Numerous moles by the patient's own estimate. The patient says their skin reddens with sun exposure. By self-report, a history of sunbed use. A clinical photograph of a skin lesion. Acquired for a research image collection, with no referral diagnosis. A female patient age 26 — 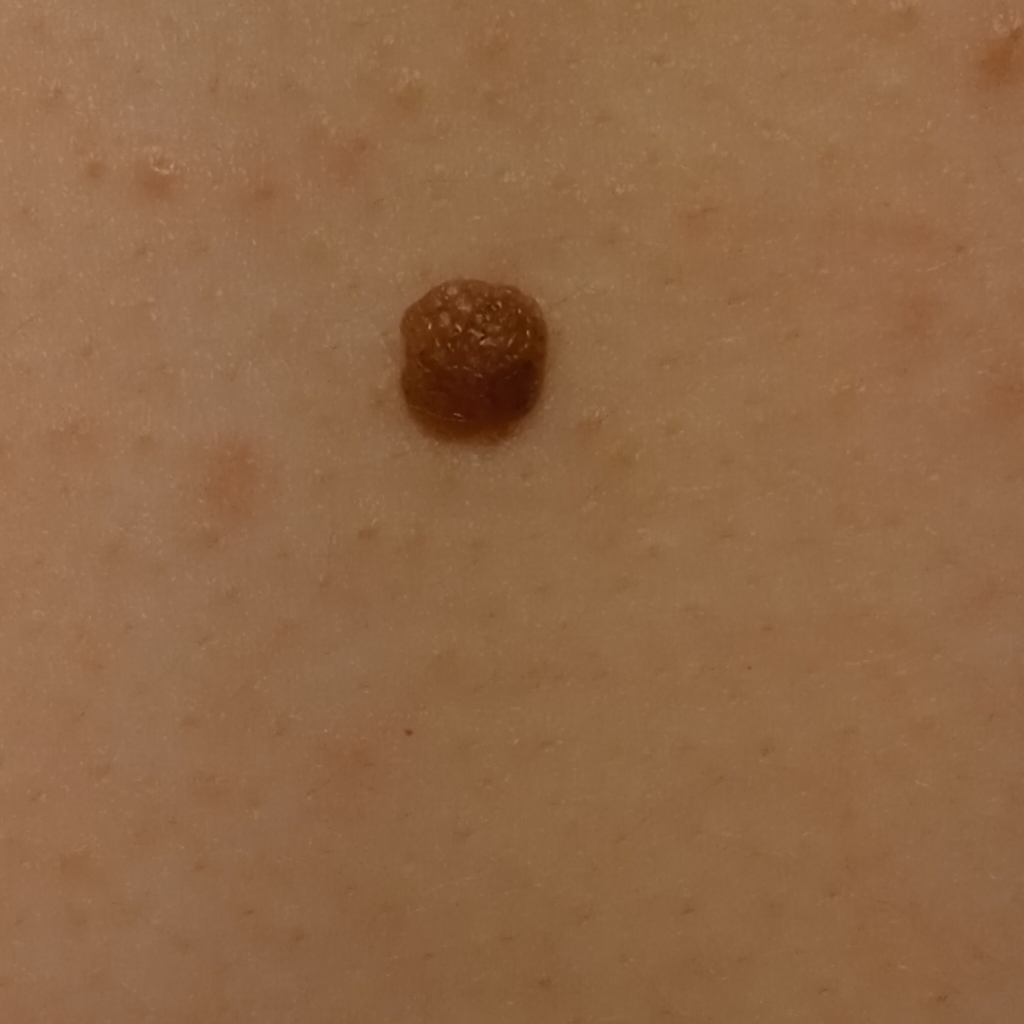The lesion is located on the back.
The lesion is about 5.6 mm across.
Dermatologist review favored a melanocytic nevus.